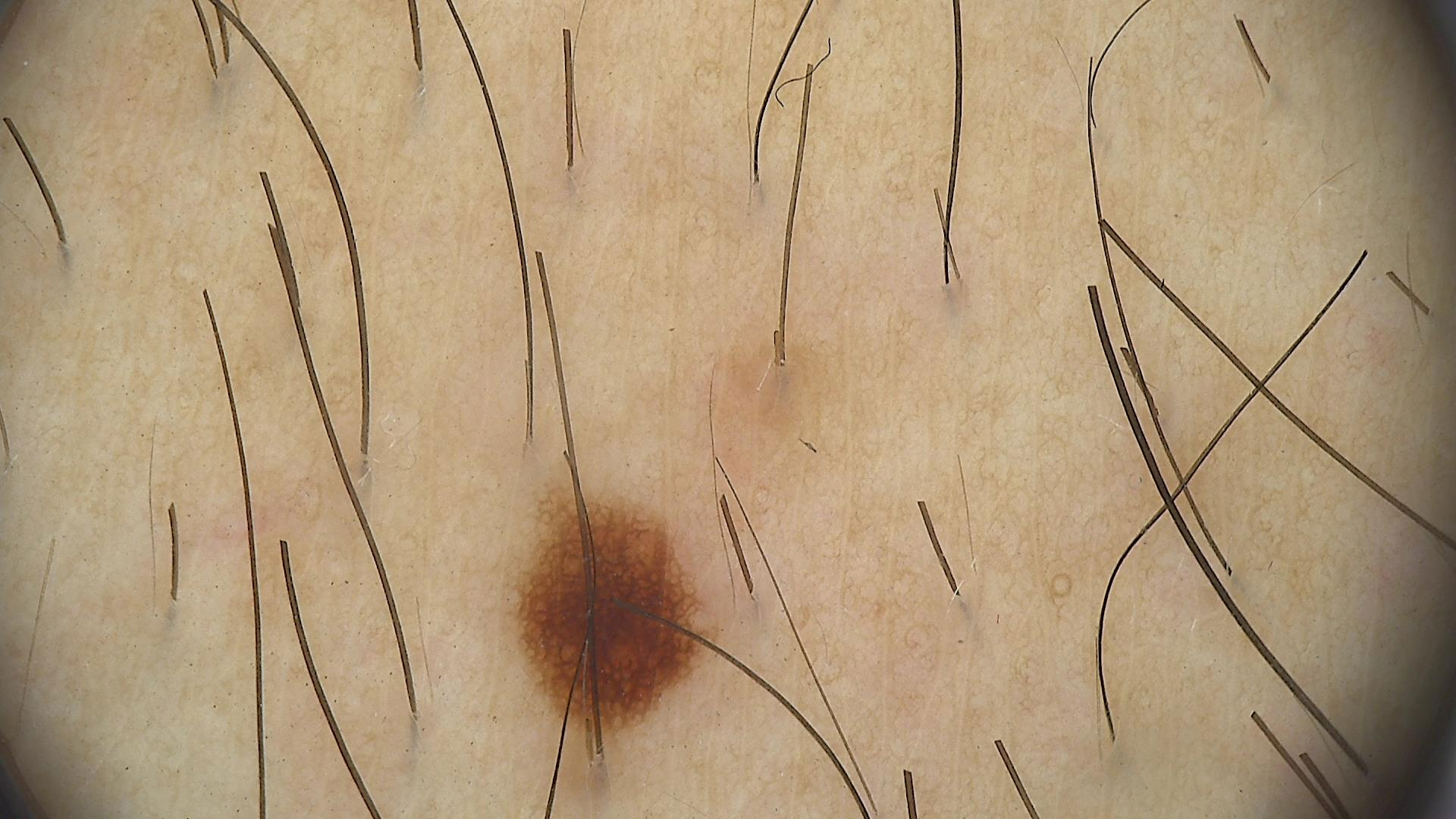• image: dermatoscopy
• diagnostic label: junctional nevus (expert consensus)